A dermoscopic close-up of a skin lesion.
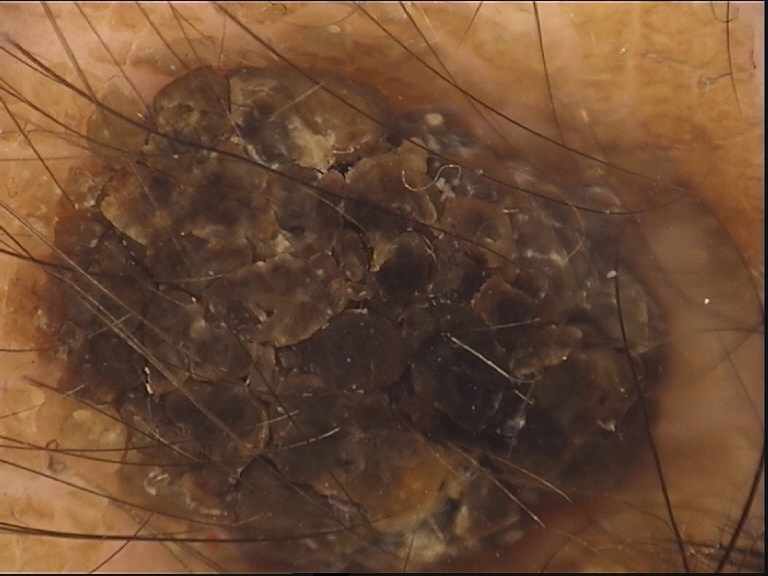assessment: seborrheic keratosis (expert consensus)